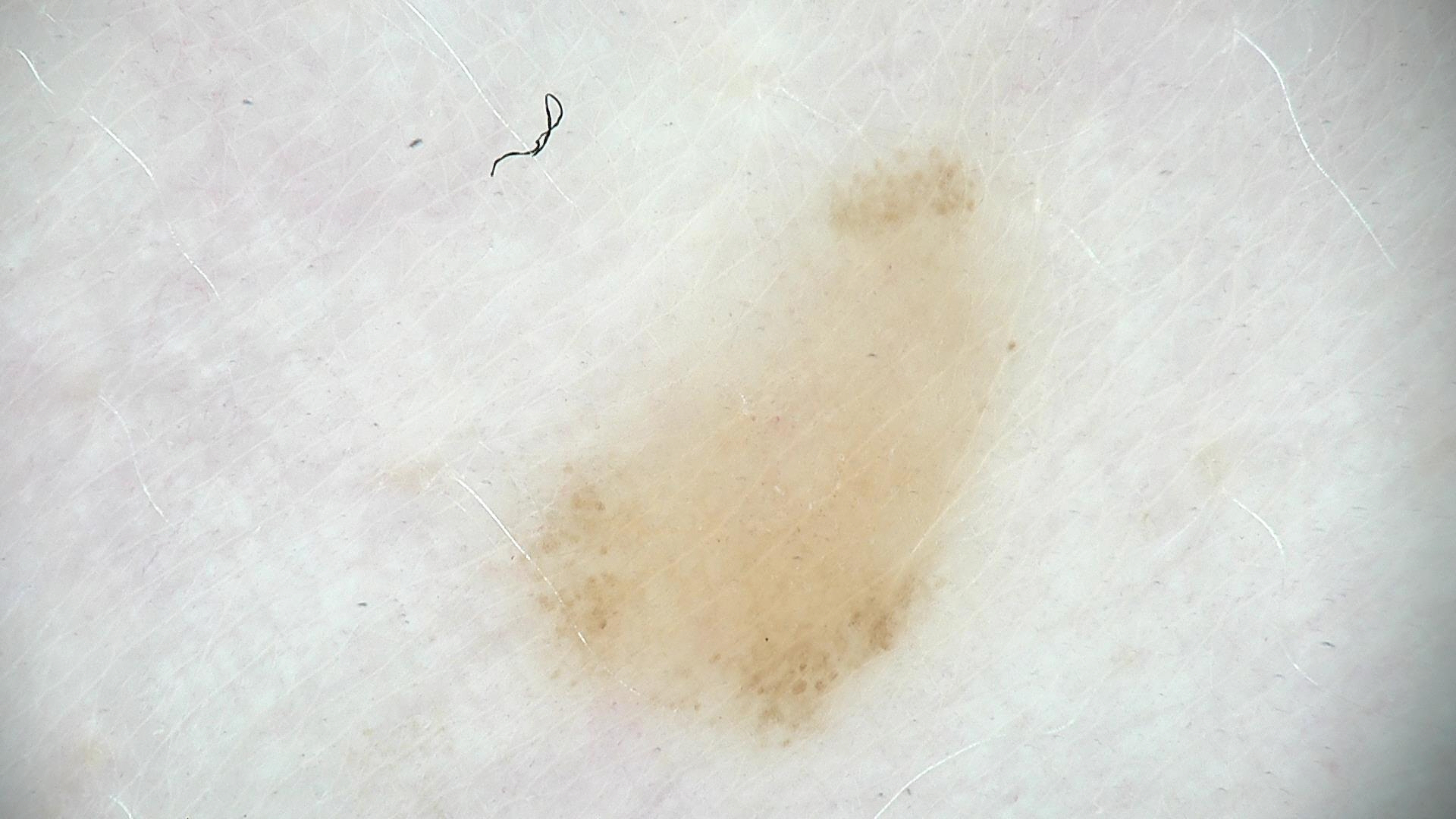Impression:
The diagnosis was a benign lesion — a dysplastic junctional nevus.